A female subject in their 90s · the patient was assessed as Fitzpatrick phototype I · a clinical photograph showing a skin lesion · by history, prior malignancy (patient or family).
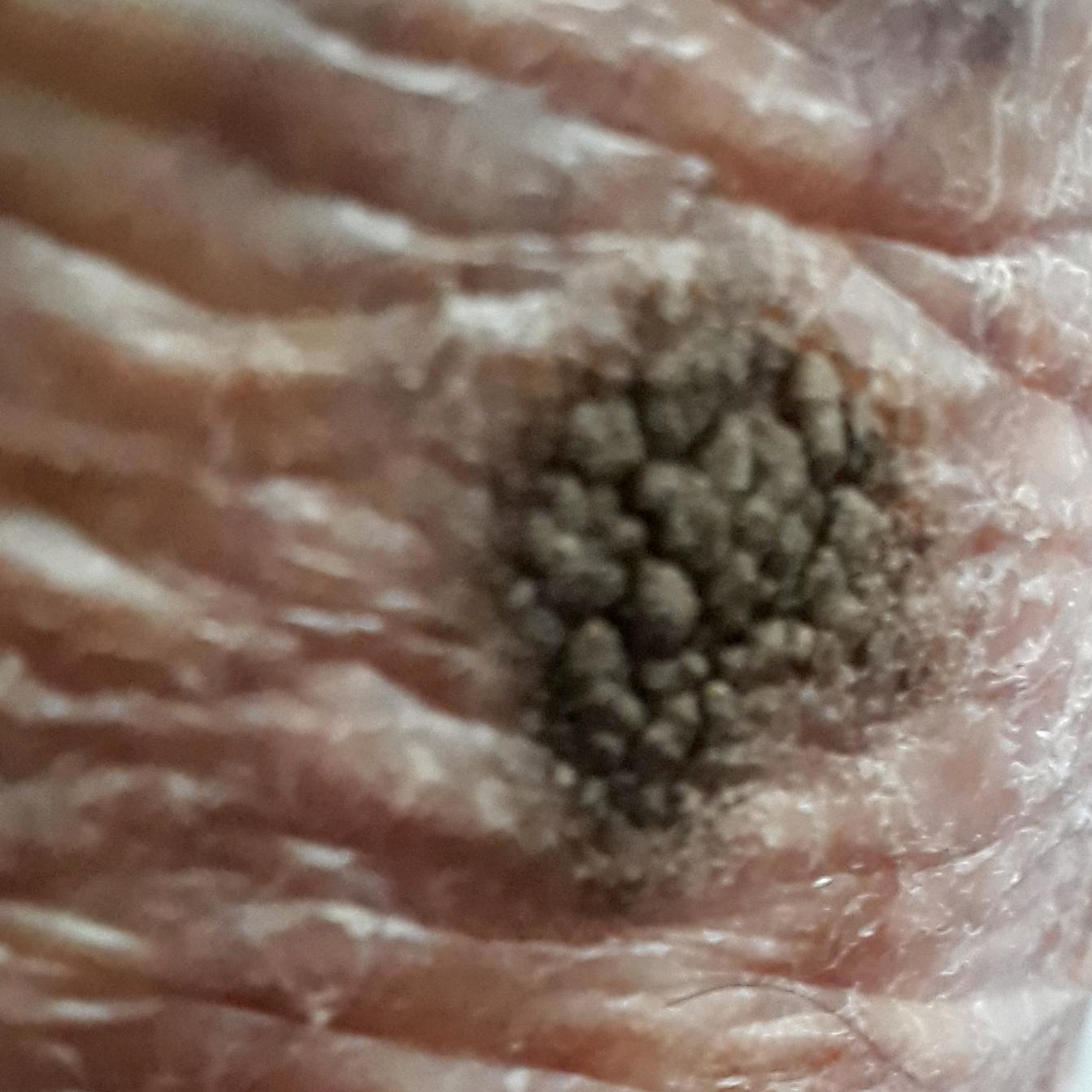Summary: The patient describes that the lesion has grown and is elevated. Conclusion: Diagnosed by dermatologist consensus as a benign lesion — a seborrheic keratosis.